A skin lesion imaged with a dermatoscope.
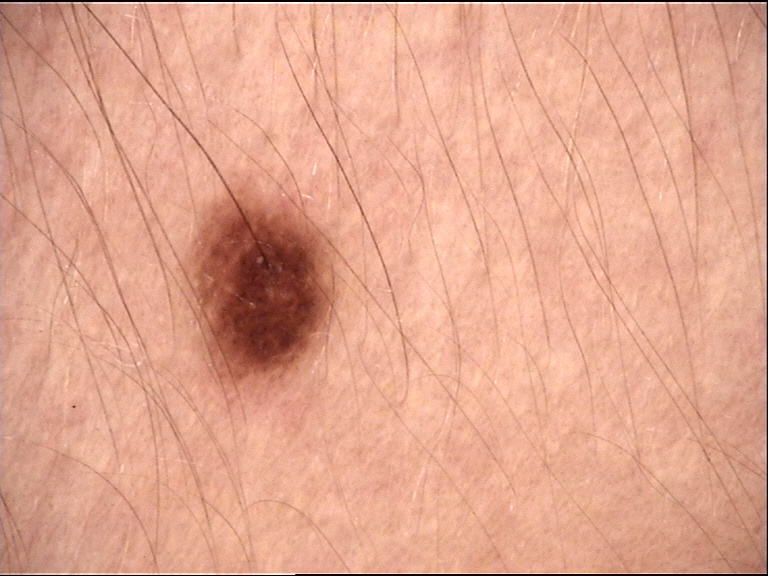The diagnosis was a banal lesion — a junctional nevus.